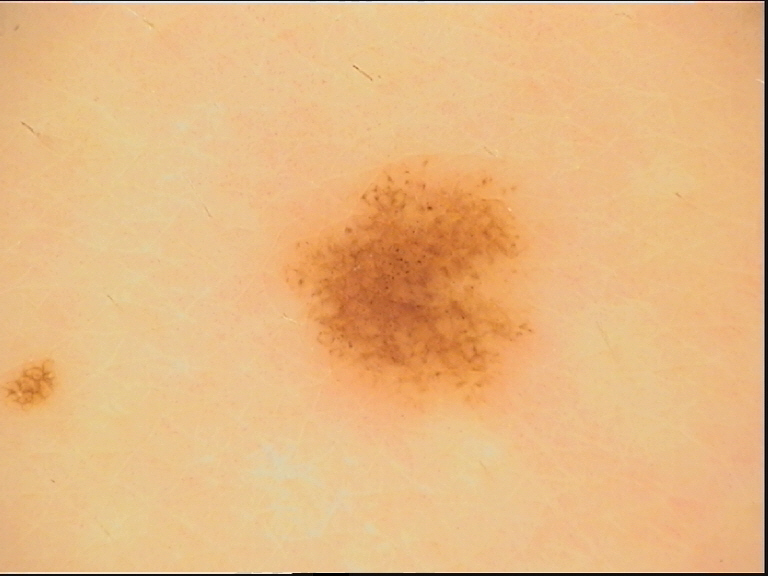image=dermoscopy | diagnosis=junctional nevus (expert consensus).